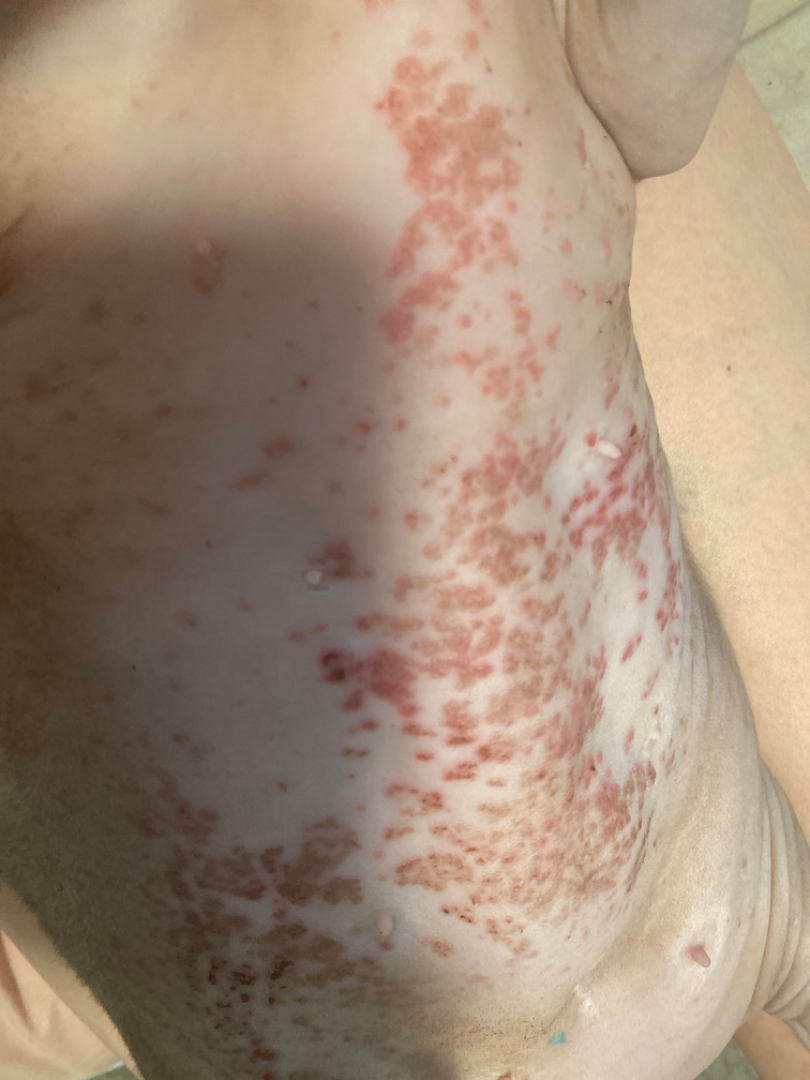Q: What was the assessment?
A: could not be assessed
Q: What is the framing?
A: at a distance